Located on the back of the hand, front of the torso, back of the torso, arm and head or neck · a close-up photograph:
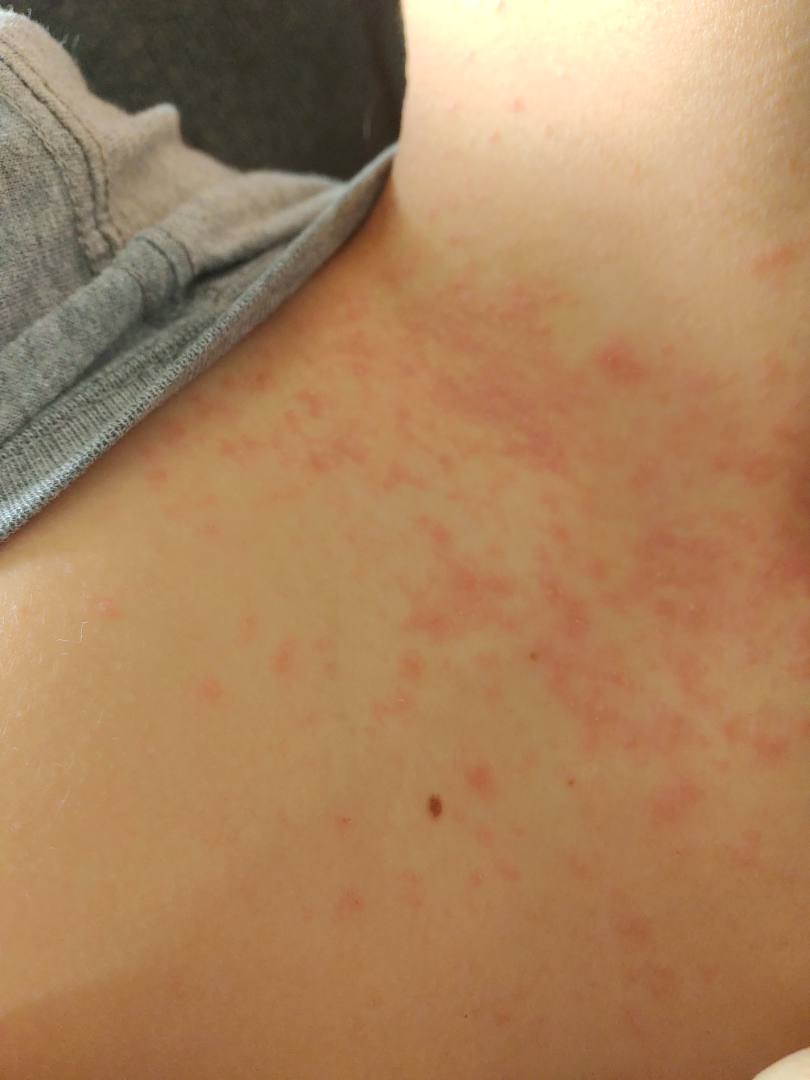assessment = unable to determine, patient's own categorization = skin that appeared healthy to them, patient-reported symptoms = itching, skin tone = FST II; lay graders estimated 3 on the Monk skin tone scale, duration = less than one week, described texture = raised or bumpy and rough or flaky.